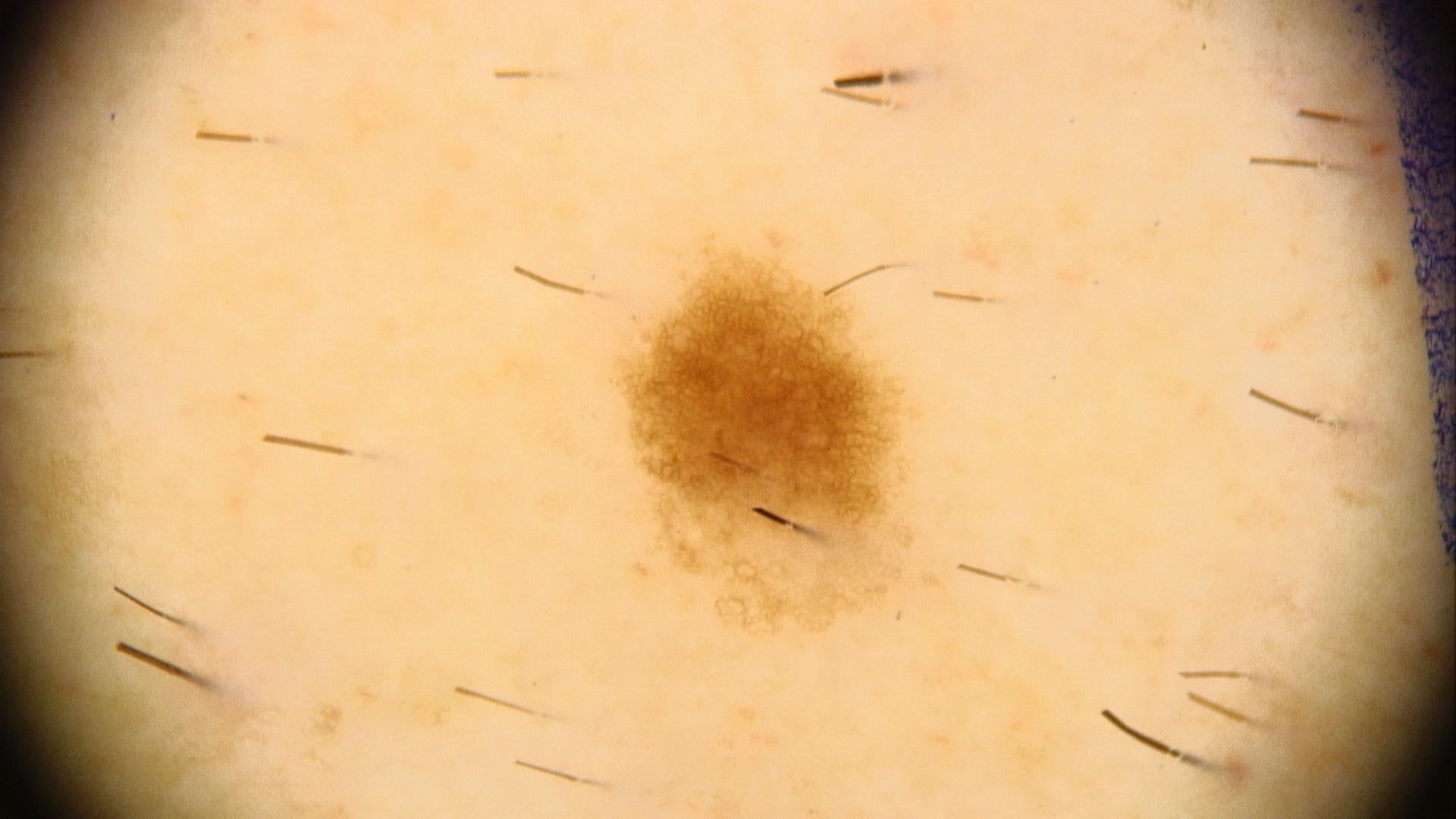{"patient": {"age_approx": 60, "sex": "male"}, "melanoma_history": {"personal_hx_melanoma": true}, "image": "contact-polarized dermoscopy", "lesion_location": {"region": "the trunk"}, "diagnosis": {"name": "Nevus", "malignancy": "benign", "confirmation": "expert clinical impression", "lineage": "melanocytic"}}